A dermoscopic close-up of a skin lesion.
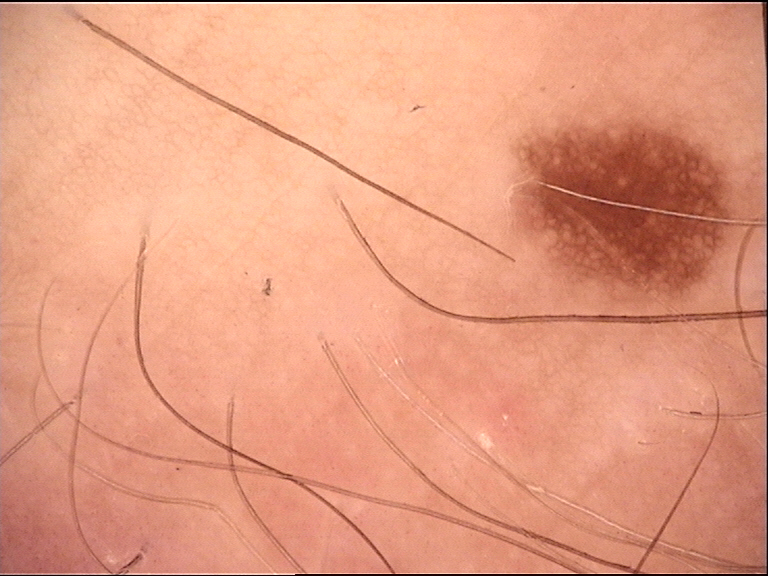diagnosis:
  name: dysplastic junctional nevus
  code: jd
  malignancy: benign
  super_class: melanocytic
  confirmation: expert consensus